A dermoscopy image of a single skin lesion.
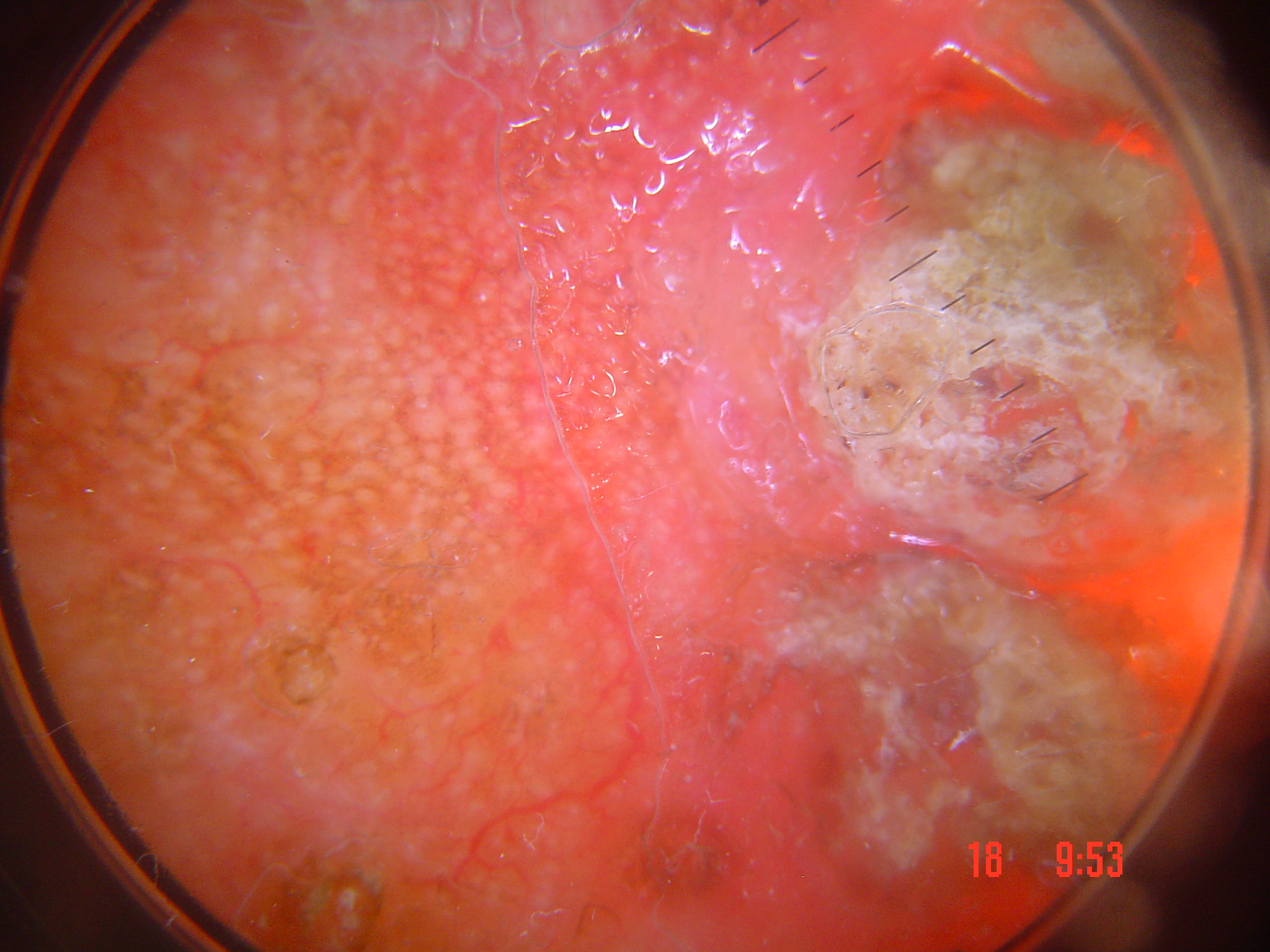Confirmed on histopathology as a keratinocytic lesion — a squamous cell carcinoma.